The lesion involves the back of the hand, a close-up photograph:
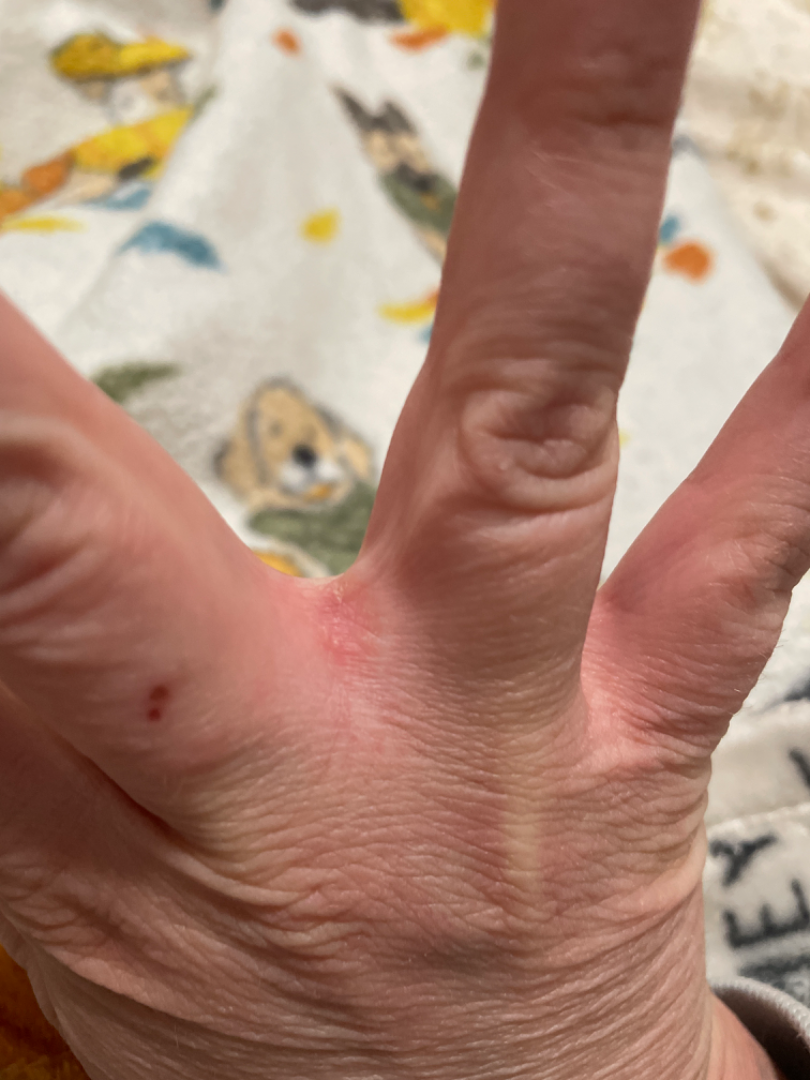<case>
<differential>
  <leading>Irritant Contact Dermatitis</leading>
</differential>
</case>